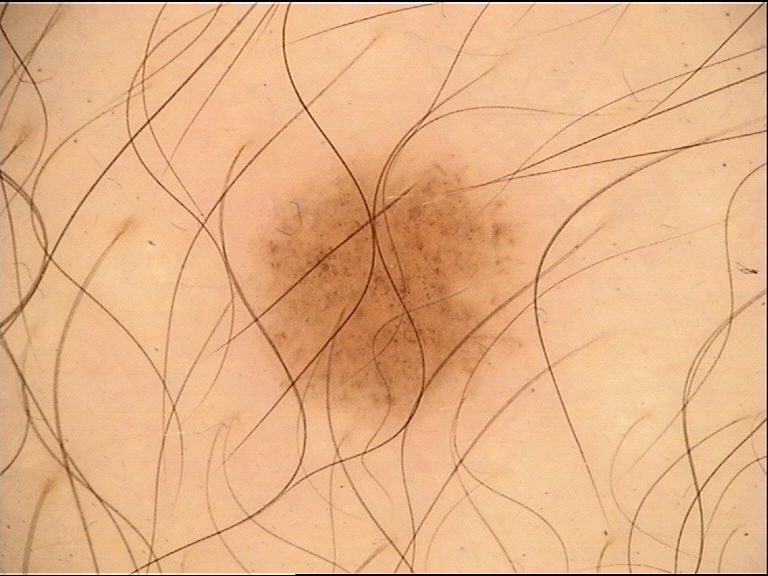Summary:
A dermatoscopic image of a skin lesion. The morphology is that of a banal lesion.
Impression:
The diagnosis was a junctional nevus.